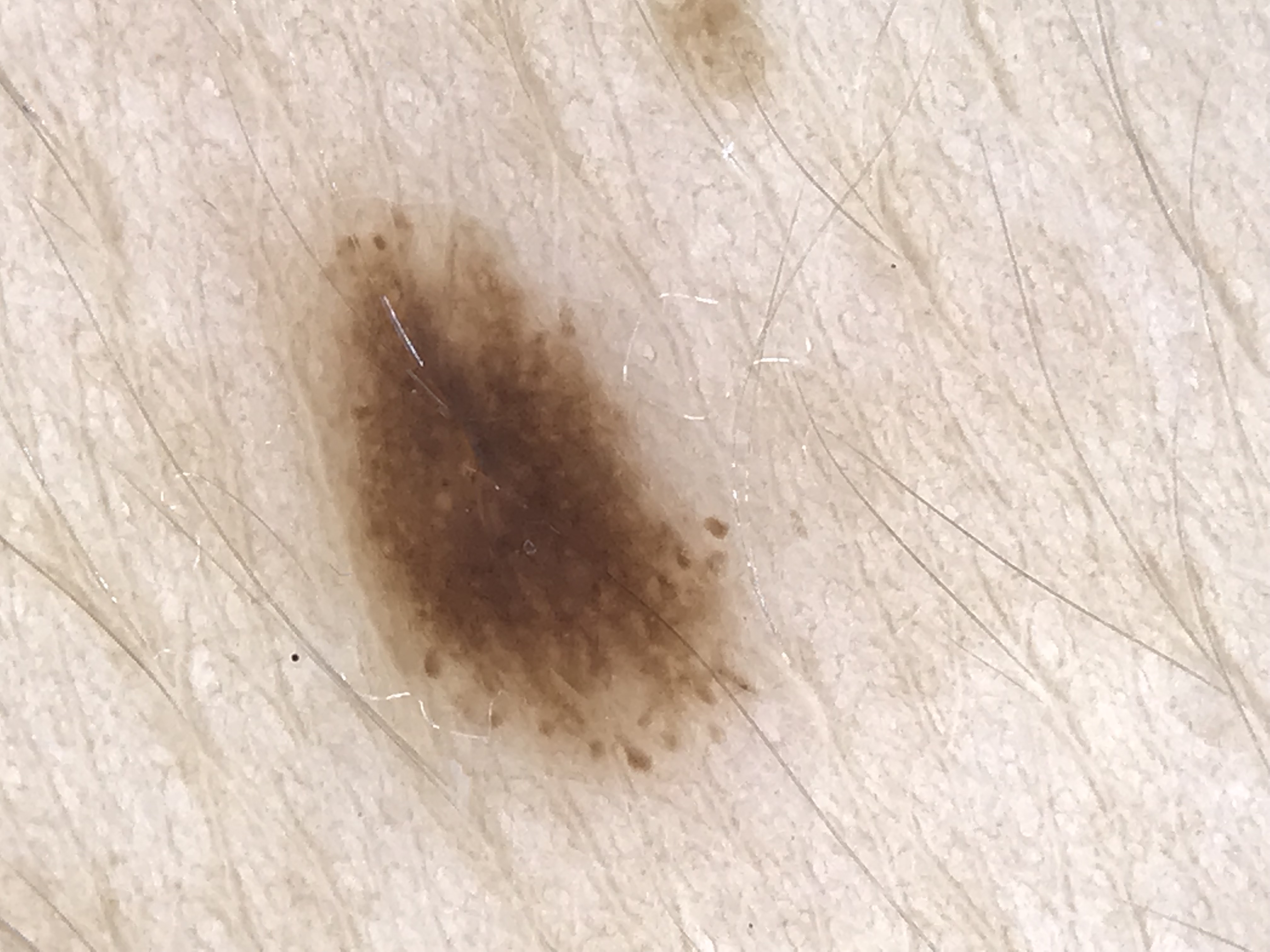A dermoscopic close-up of a skin lesion.
Labeled as a dysplastic junctional nevus.